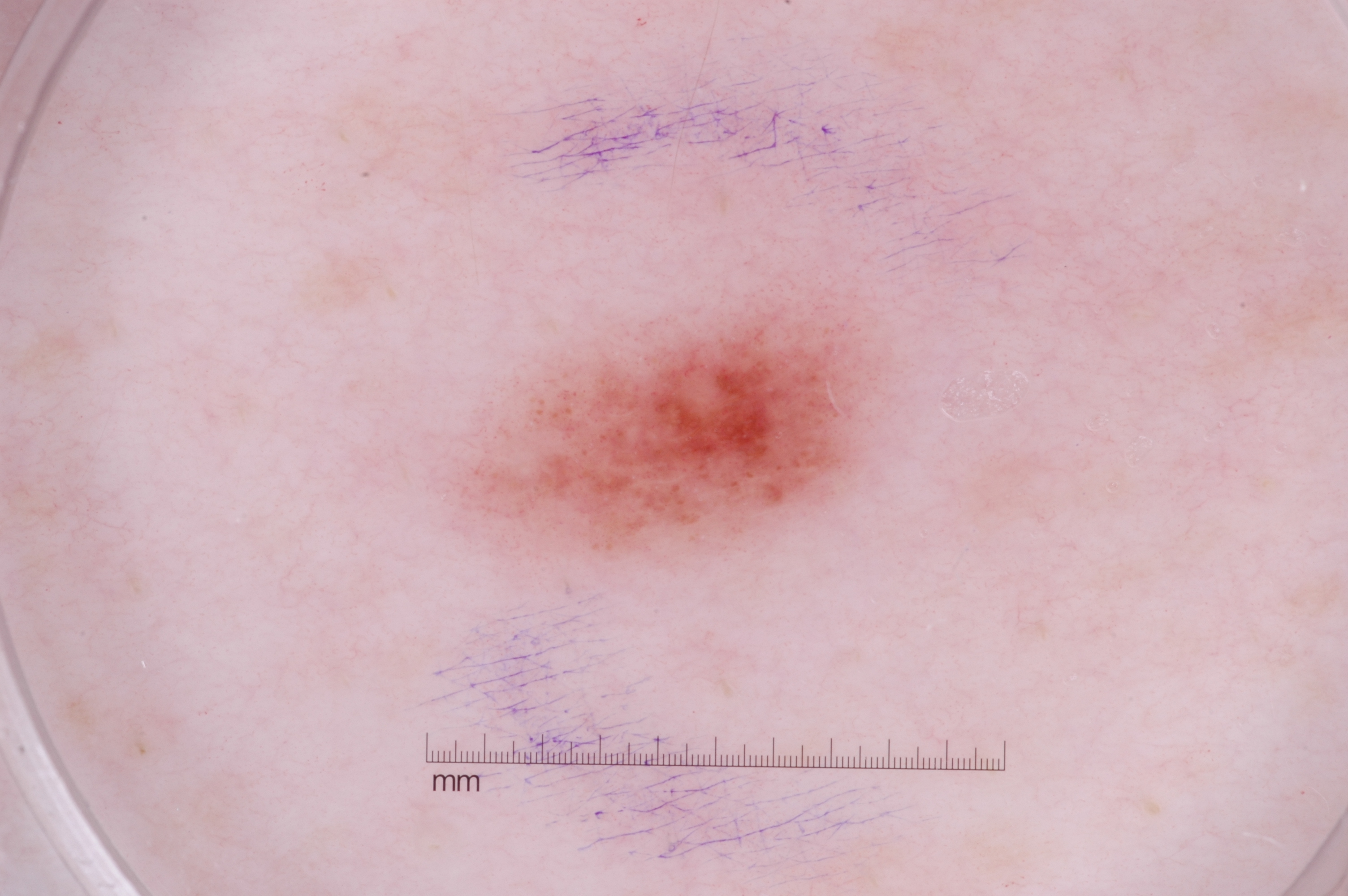imaging = dermoscopic image
subject = male, in their mid- to late 40s
absent dermoscopic findings = negative network, streaks, milia-like cysts, and pigment network
lesion bbox = <box>453, 287, 885, 567</box>
lesion extent = ~7% of the field
diagnosis = a melanocytic nevus, a benign lesion